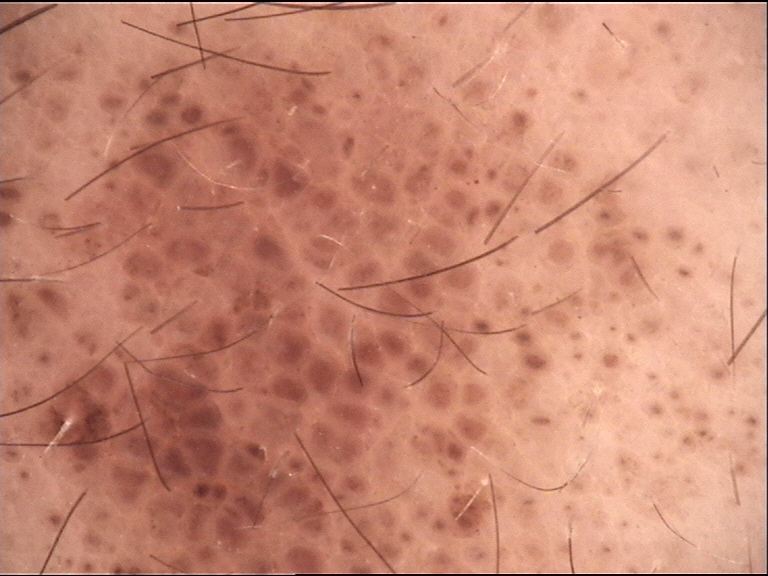A skin lesion imaged with a dermatoscope. The architecture is that of a banal lesion. The diagnostic label was a congenital compound nevus.